The patient considered this a rash; the patient notes the condition has been present for one to four weeks; symptoms reported: bothersome appearance, darkening, enlargement and itching; skin tone: FST V; the lesion involves the head or neck; the photograph was taken at a distance; no constitutional symptoms were reported: 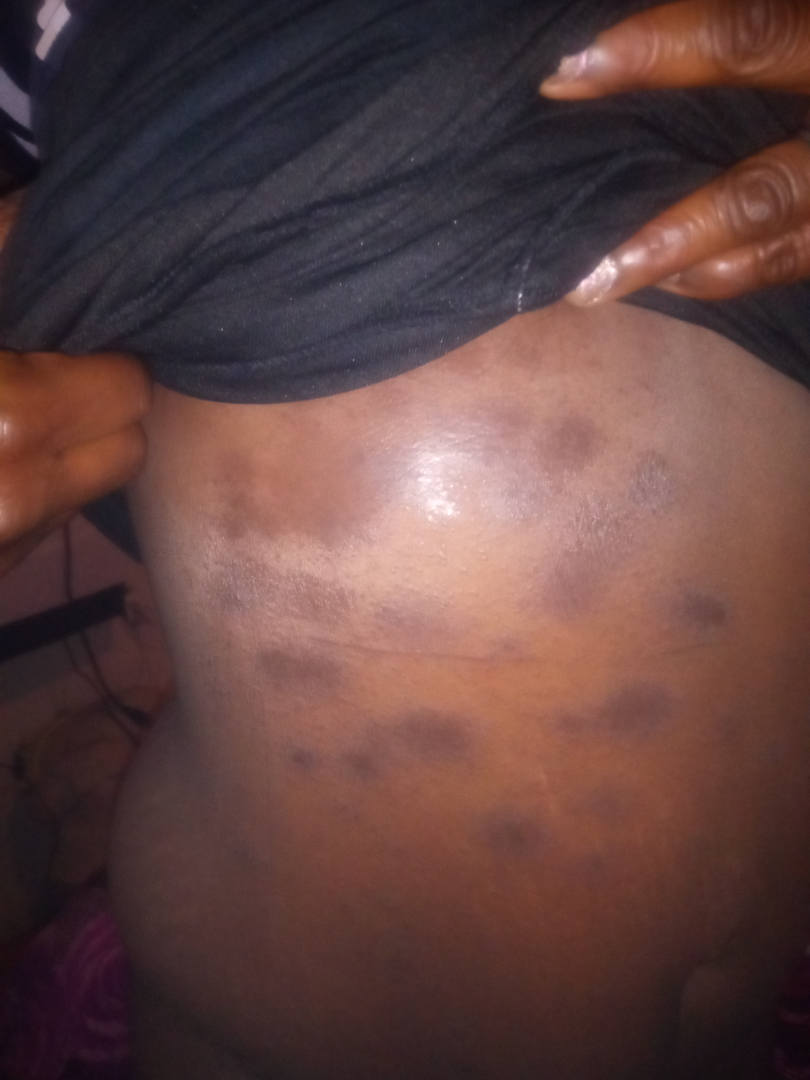assessment: indeterminate from the photograph.